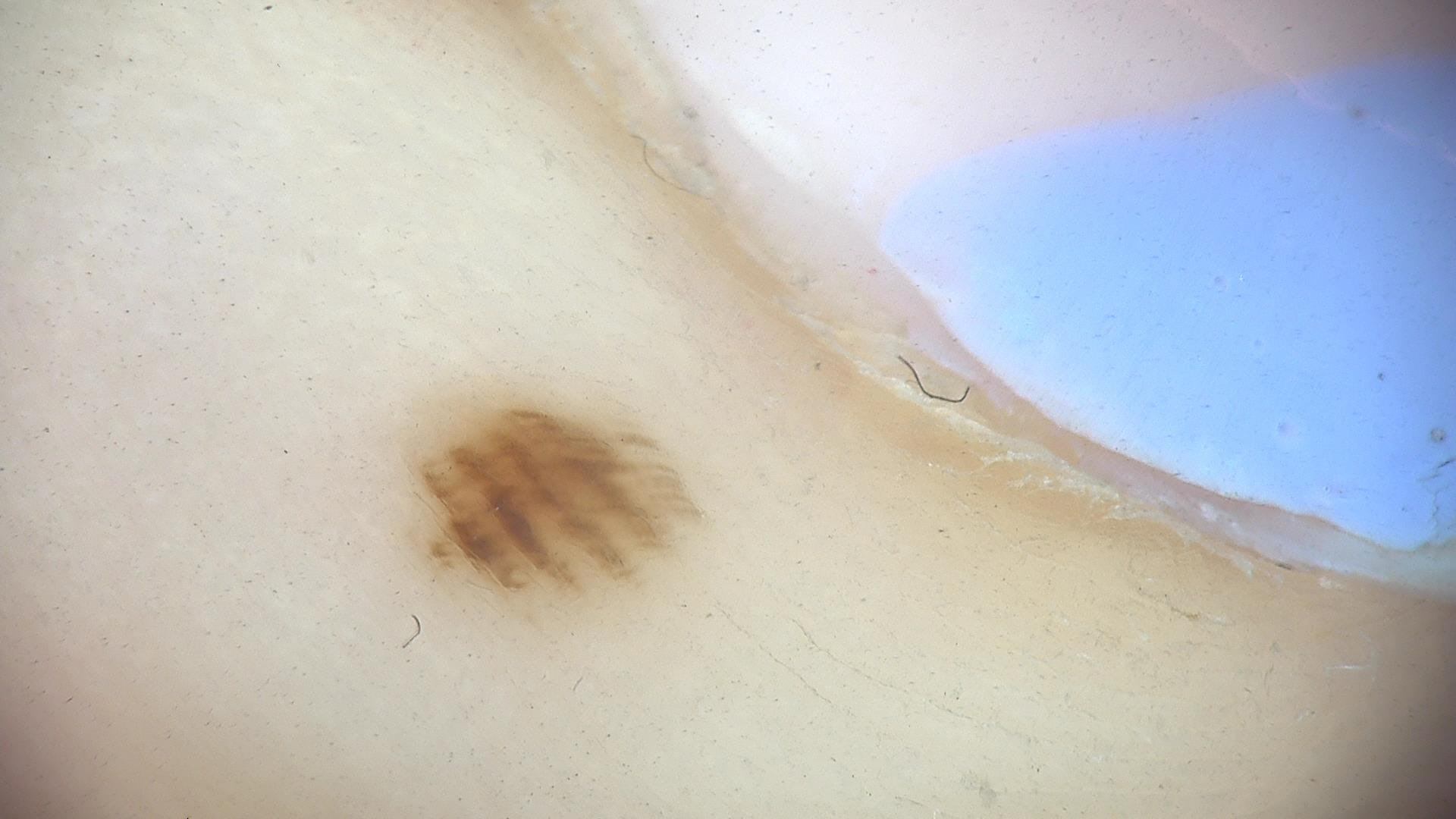Conclusion:
Classified as an acral dysplastic junctional nevus.